The photo was captured at a distance, located on the leg:
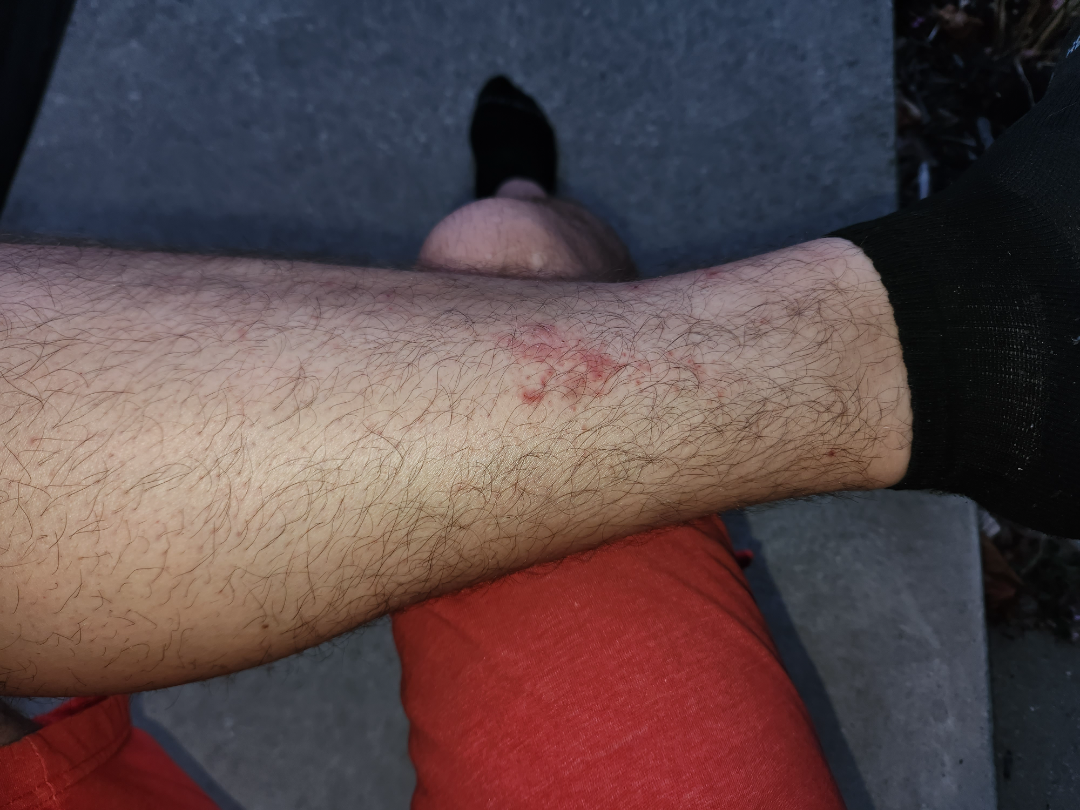assessment = could not be assessed.